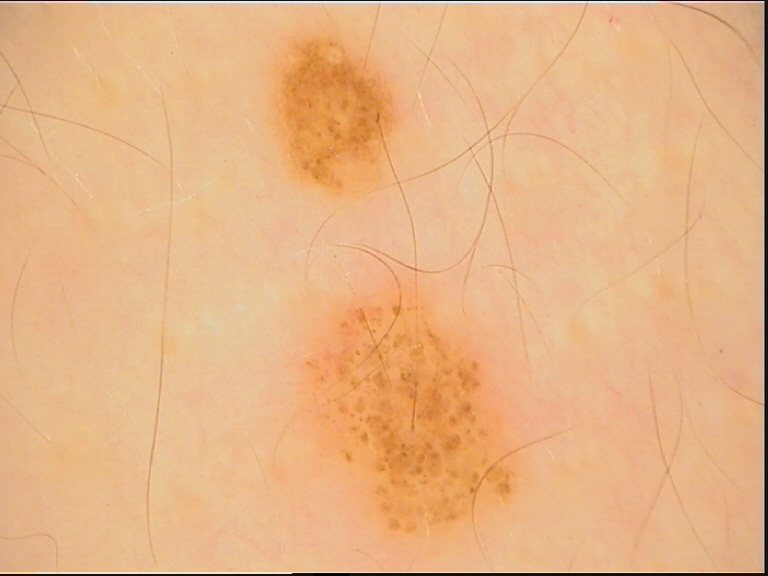Impression: Classified as a benign lesion — a dysplastic compound nevus.